The affected area is the arm; the contributor is a male aged 50–59; this is a close-up image: 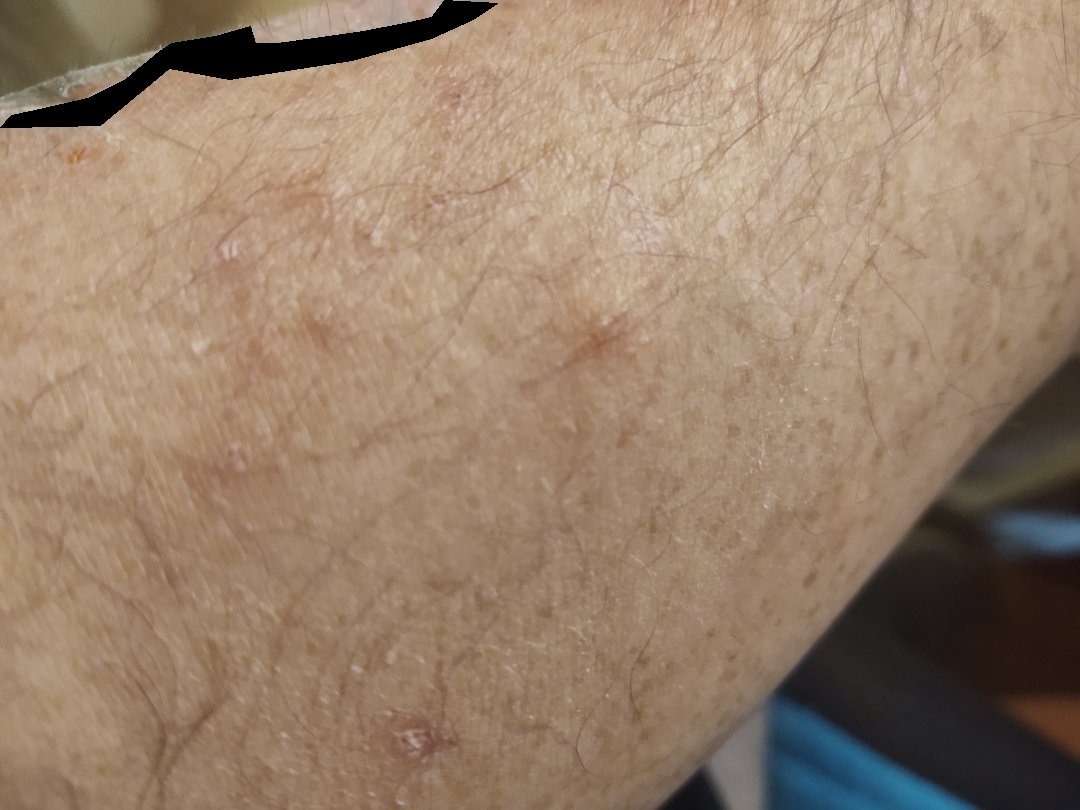The patient considered this a rash. The patient notes the lesion is raised or bumpy. The patient reported no systemic symptoms. Present for less than one week. The patient notes itching and bothersome appearance. One reviewing dermatologist: most consistent with Folliculitis; with consideration of Irritant Contact Dermatitis.